A dermoscopic image of a skin lesion:
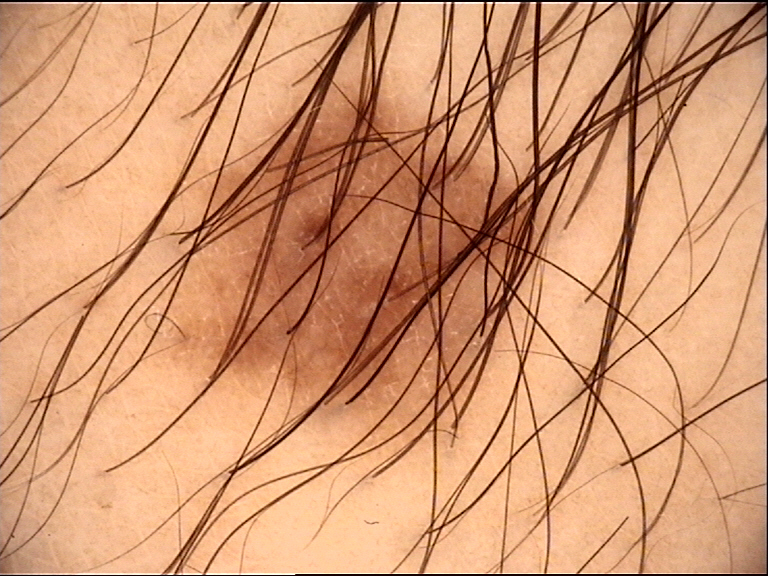category: banal, diagnosis: junctional nevus (expert consensus).